The subject is a female aged 30–39; the photo was captured at an angle; the front of the torso is involved: 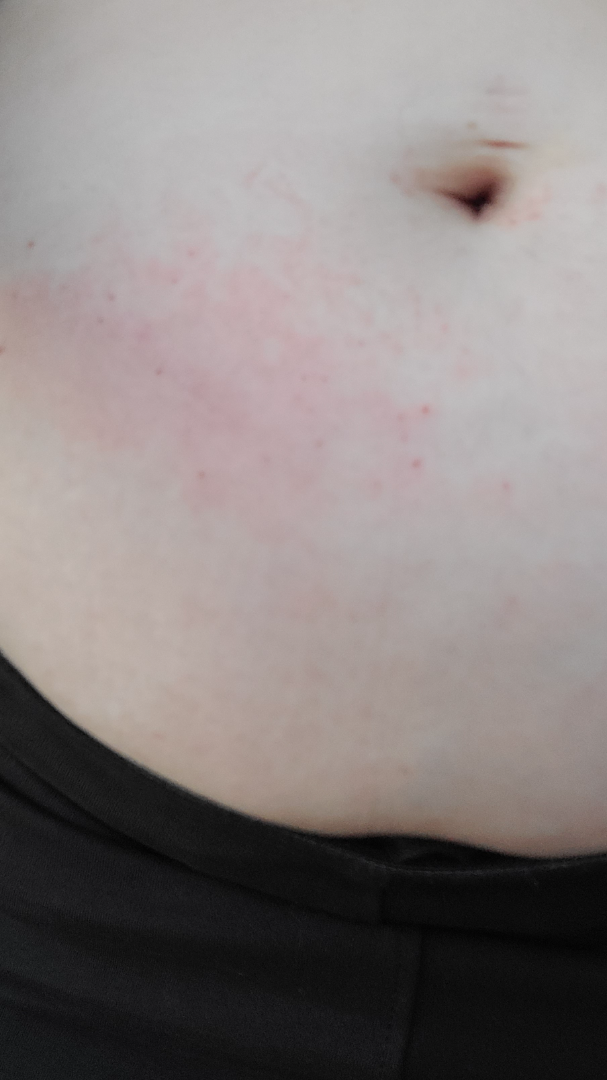The skin findings could not be characterized from the image.